This image was taken at an angle, the lesion involves the leg.
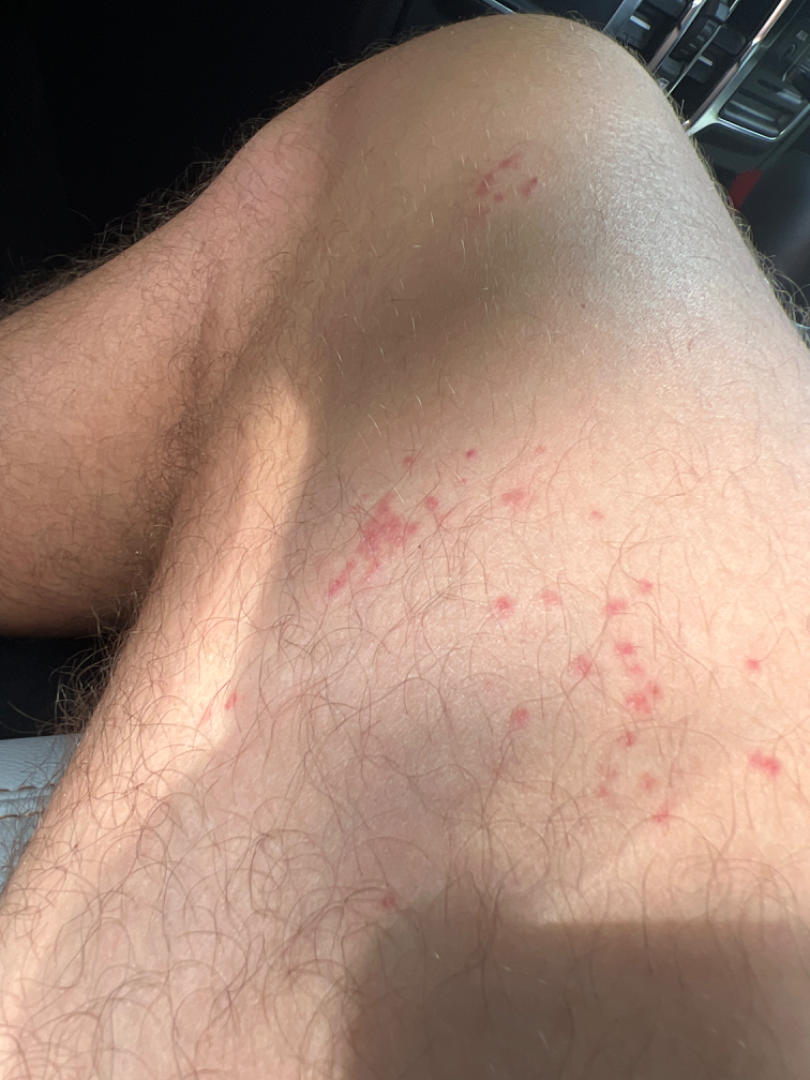{
  "assessment": "indeterminate from the photograph",
  "duration": "less than one week",
  "patient_category": "a rash",
  "texture": "flat"
}